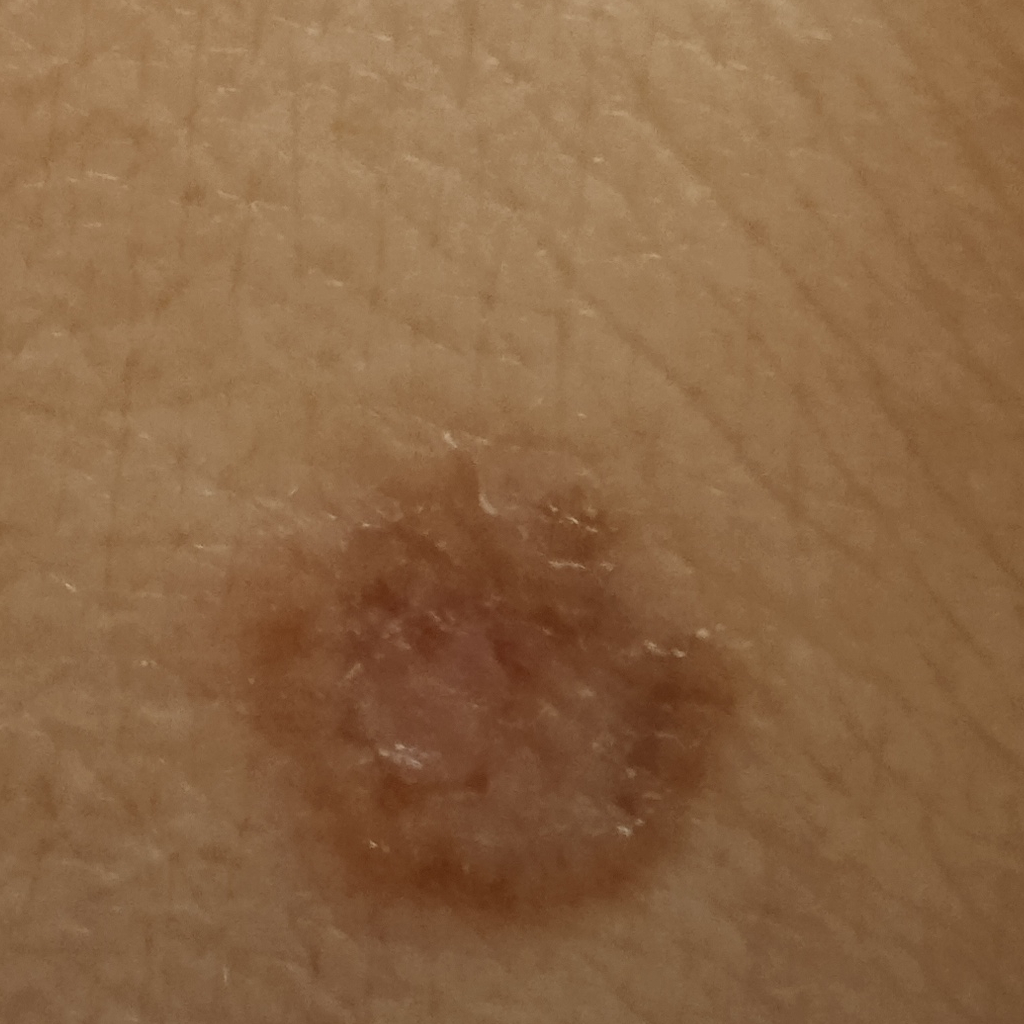A macroscopic clinical photograph of a skin lesion.
A female subject age 60.
Located on the torso.
The consensus diagnosis for this lesion was a basal cell carcinoma.